Male patient, age 60–69 · the lesion involves the front of the torso, arm, back of the hand and leg · this image was taken at a distance:
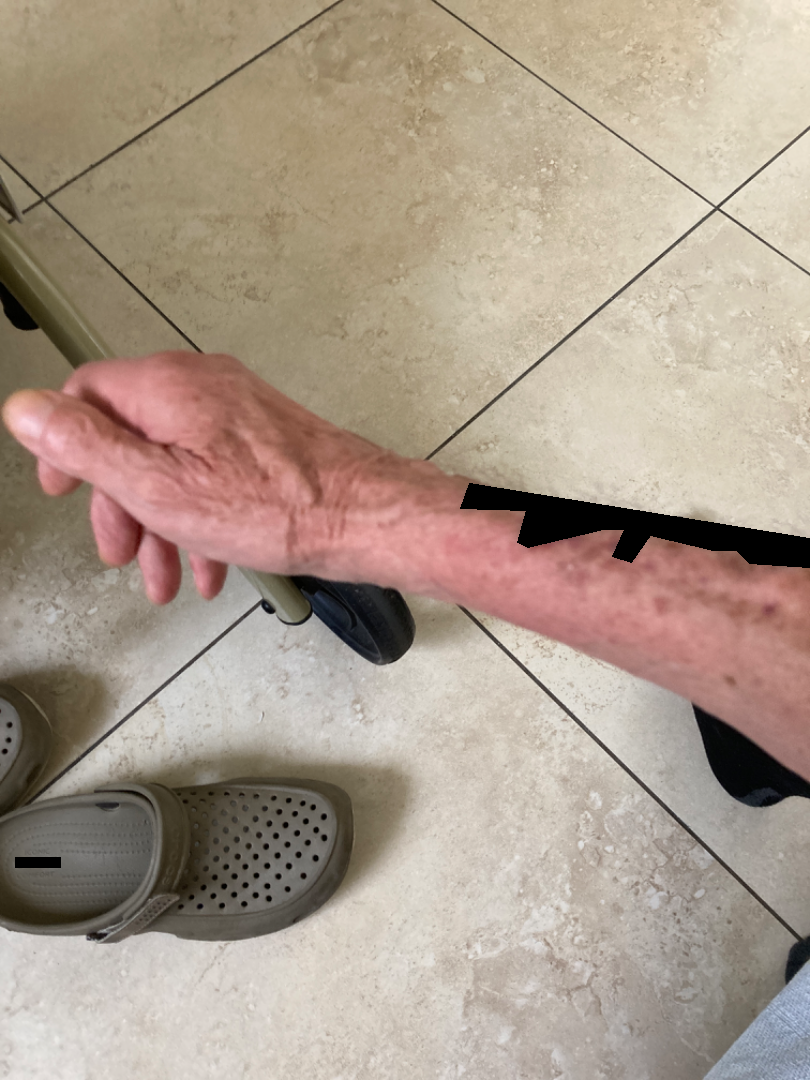The reviewer was unable to grade this case for skin condition. Texture is reported as raised or bumpy. The patient described the issue as a rash. Associated systemic symptoms include shortness of breath. The condition has been present for less than one week. Reported lesion symptoms include itching.